The patient indicates the lesion is rough or flaky, located on the arm, this image was taken at an angle, the patient considered this a pigmentary problem, skin tone: Fitzpatrick V; lay graders estimated MST 3–4, the patient indicates darkening: 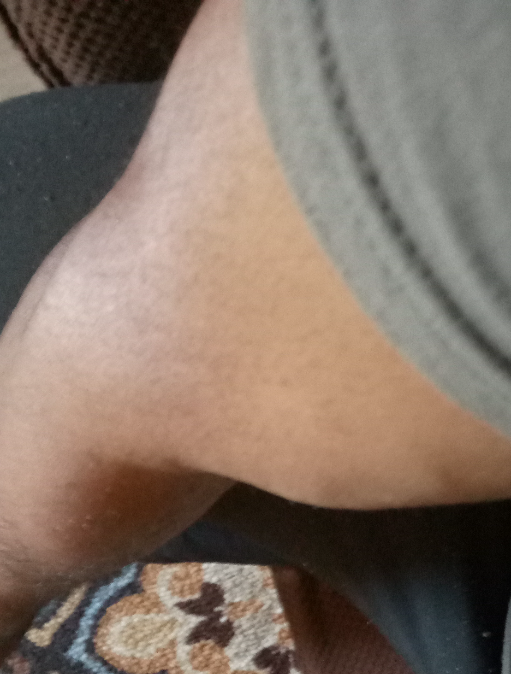Findings:
- assessment — unable to determine